The patient is female, the head or neck is involved, the photo was captured at a distance: 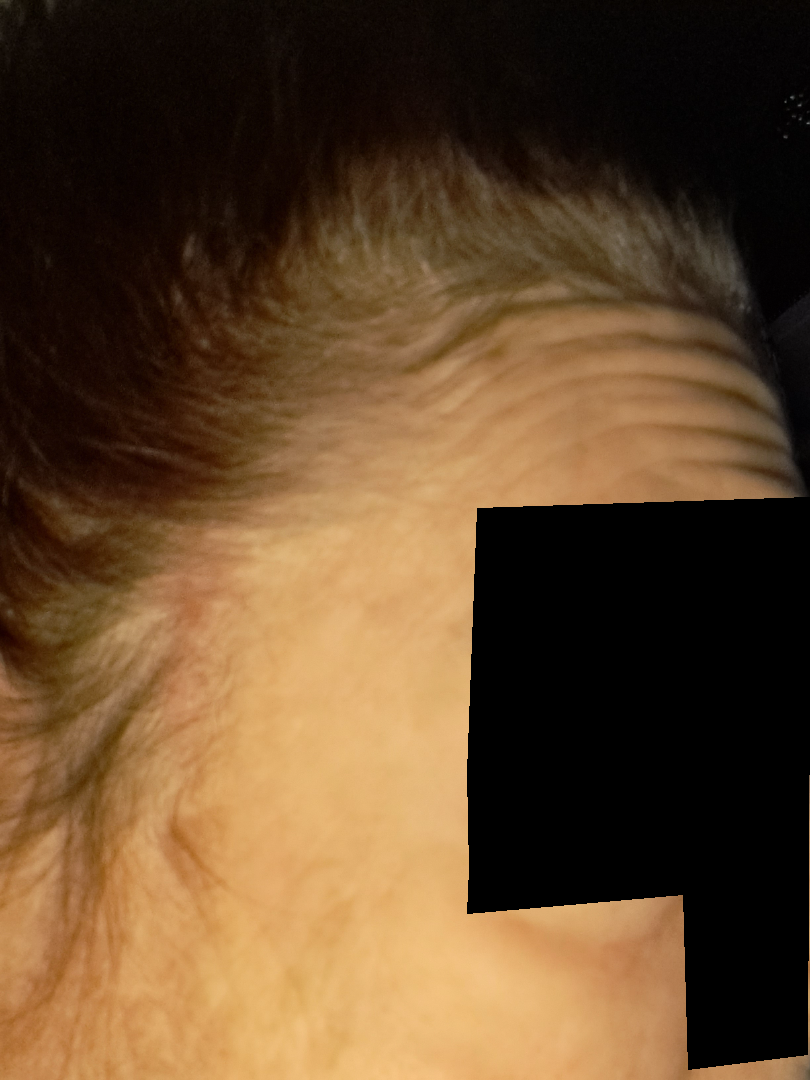The image was not sufficient for the reviewer to characterize the skin condition.